Dermoscopy of a skin lesion:
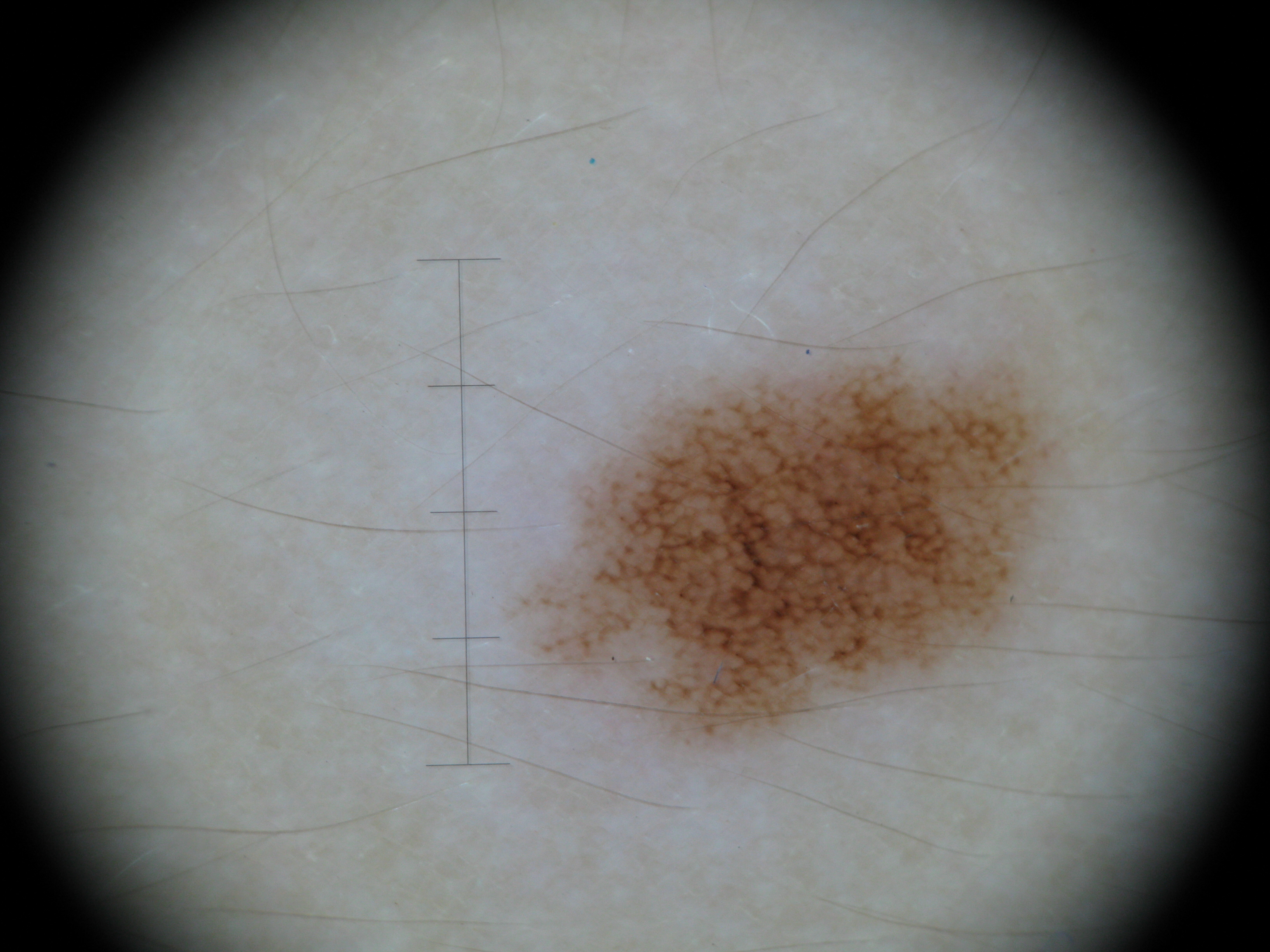Diagnosed as a benign lesion — a dysplastic junctional nevus.